A skin lesion imaged with a dermatoscope.
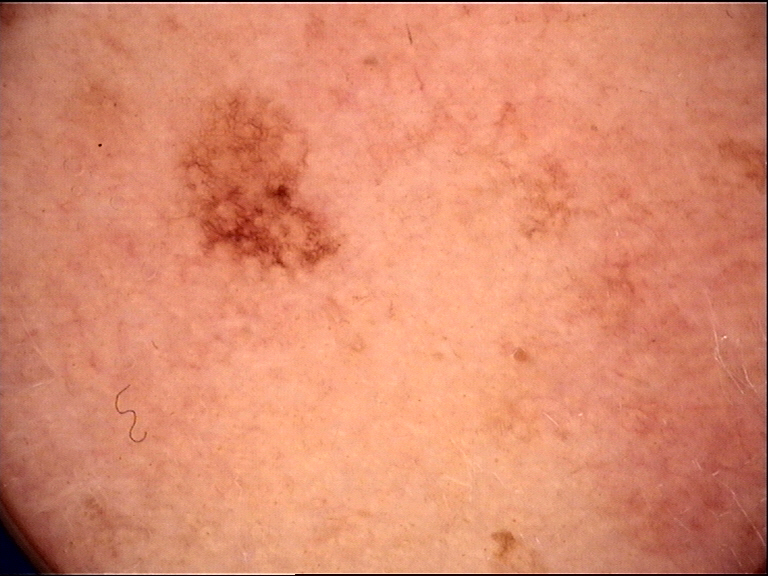– label — dysplastic junctional nevus (expert consensus)